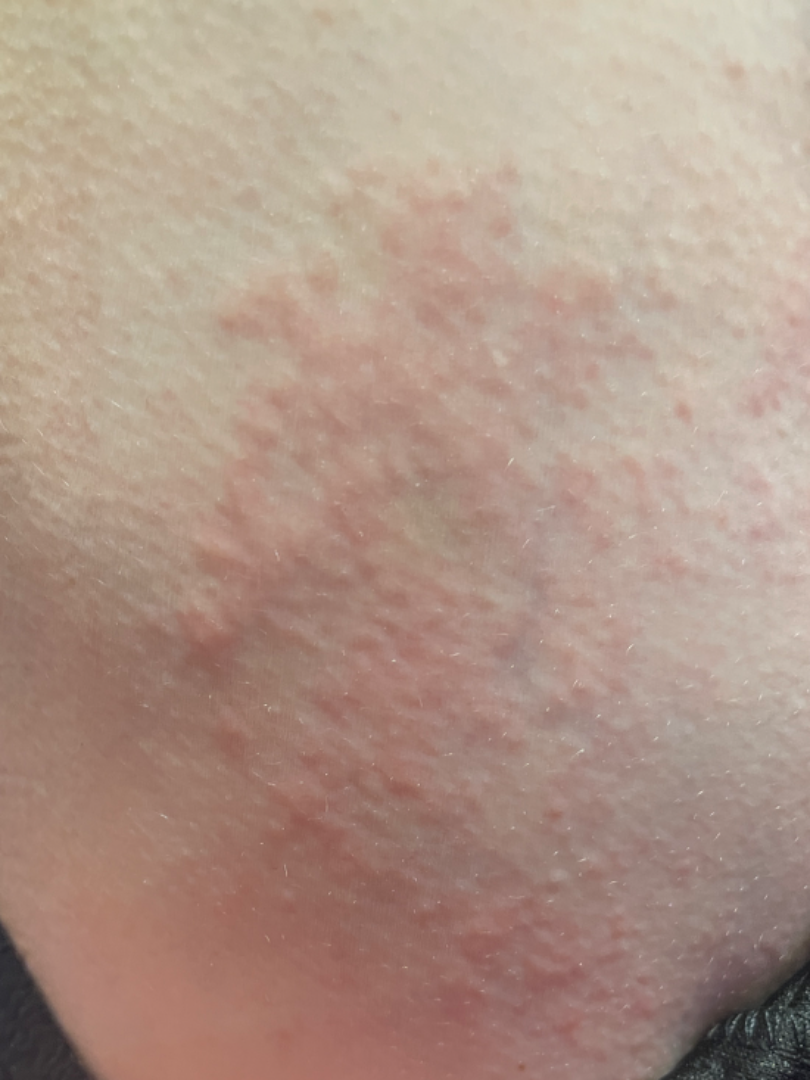Patient information:
Reported lesion symptoms include itching. The back of the torso is involved. The patient indicates associated joint pain. The patient considered this a rash. The photograph is a close-up of the affected area.
Review:
Most consistent with Acute and chronic dermatitis.